This image was taken at an angle. The contributor notes the condition has been present for less than one week. Self-categorized by the patient as a rash. The front of the torso, leg, back of the hand, head or neck and arm are involved. The subject is a female aged 30–39: 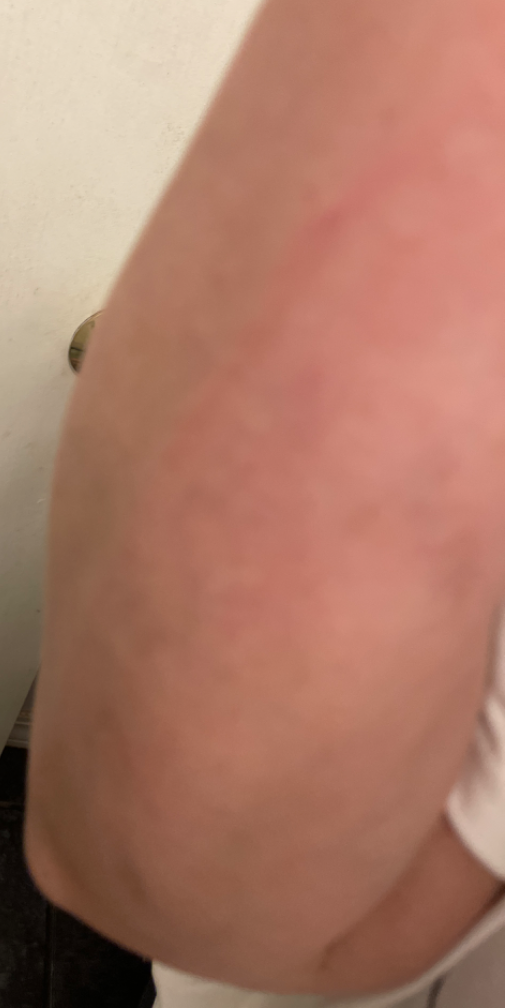Case summary:
- assessment · not assessable